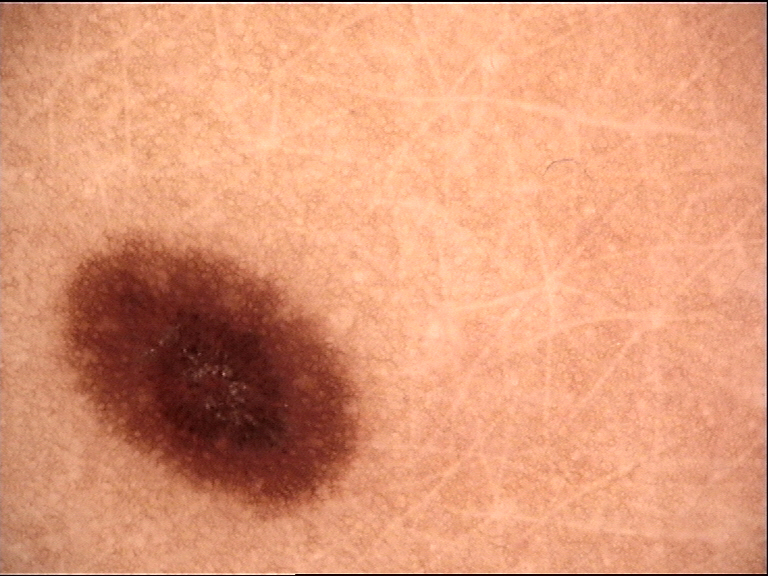A dermatoscopic image of a skin lesion. This is a banal lesion. Diagnosed as a junctional nevus.